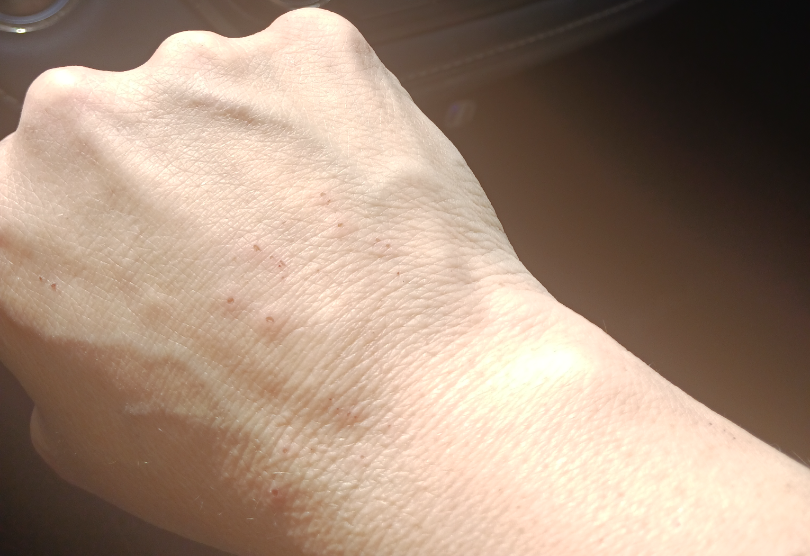* assessment · not assessable
* described texture · raised or bumpy
* patient-reported symptoms · bothersome appearance, pain, burning, itching and bleeding
* anatomic site · back of the hand, back of the torso, front of the torso and arm
* onset · one to four weeks
* patient's own categorization · a rash
* view · at a distance
* skin tone · FST IV